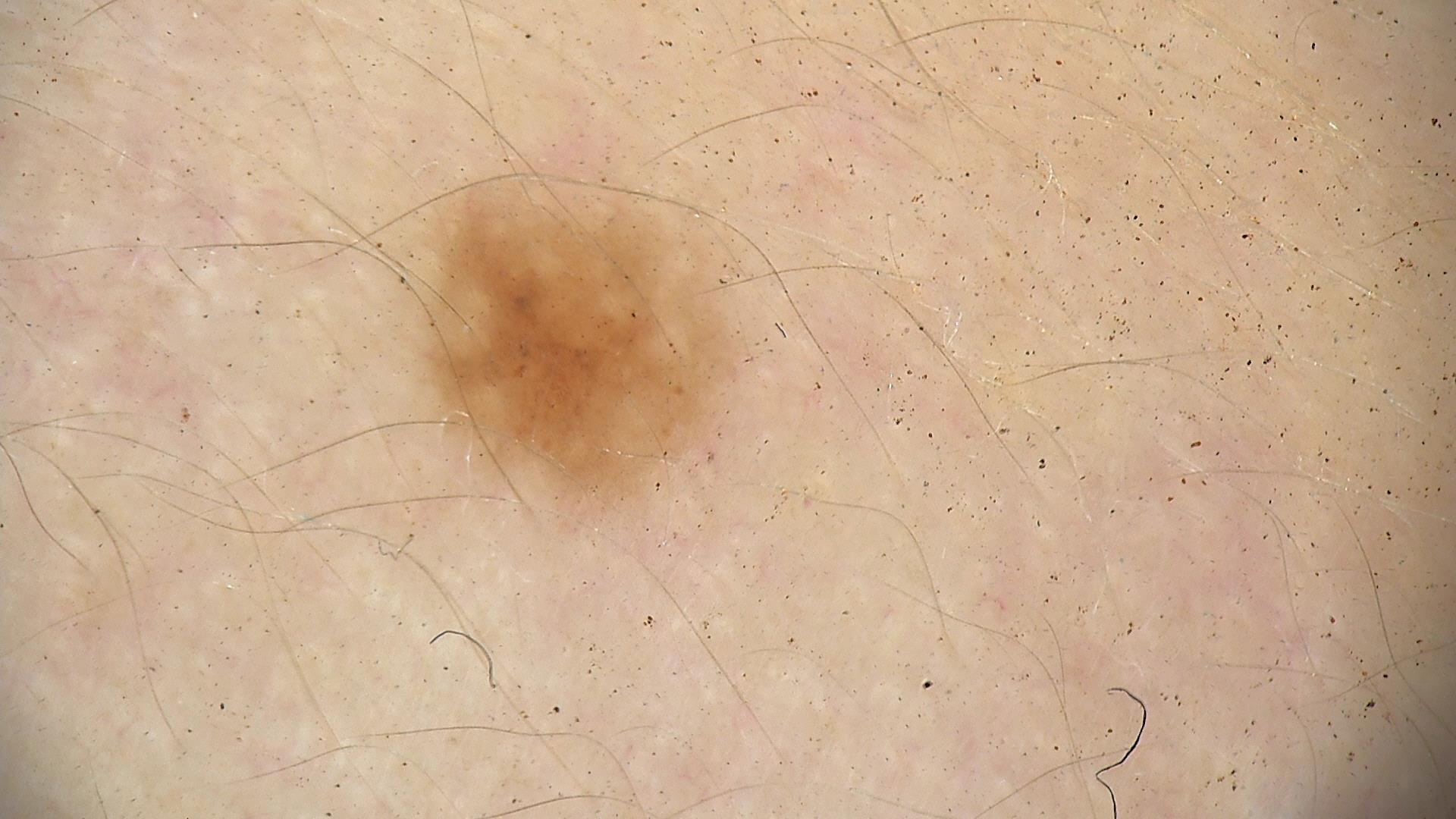Impression:
Diagnosed as a benign lesion — a dysplastic junctional nevus.